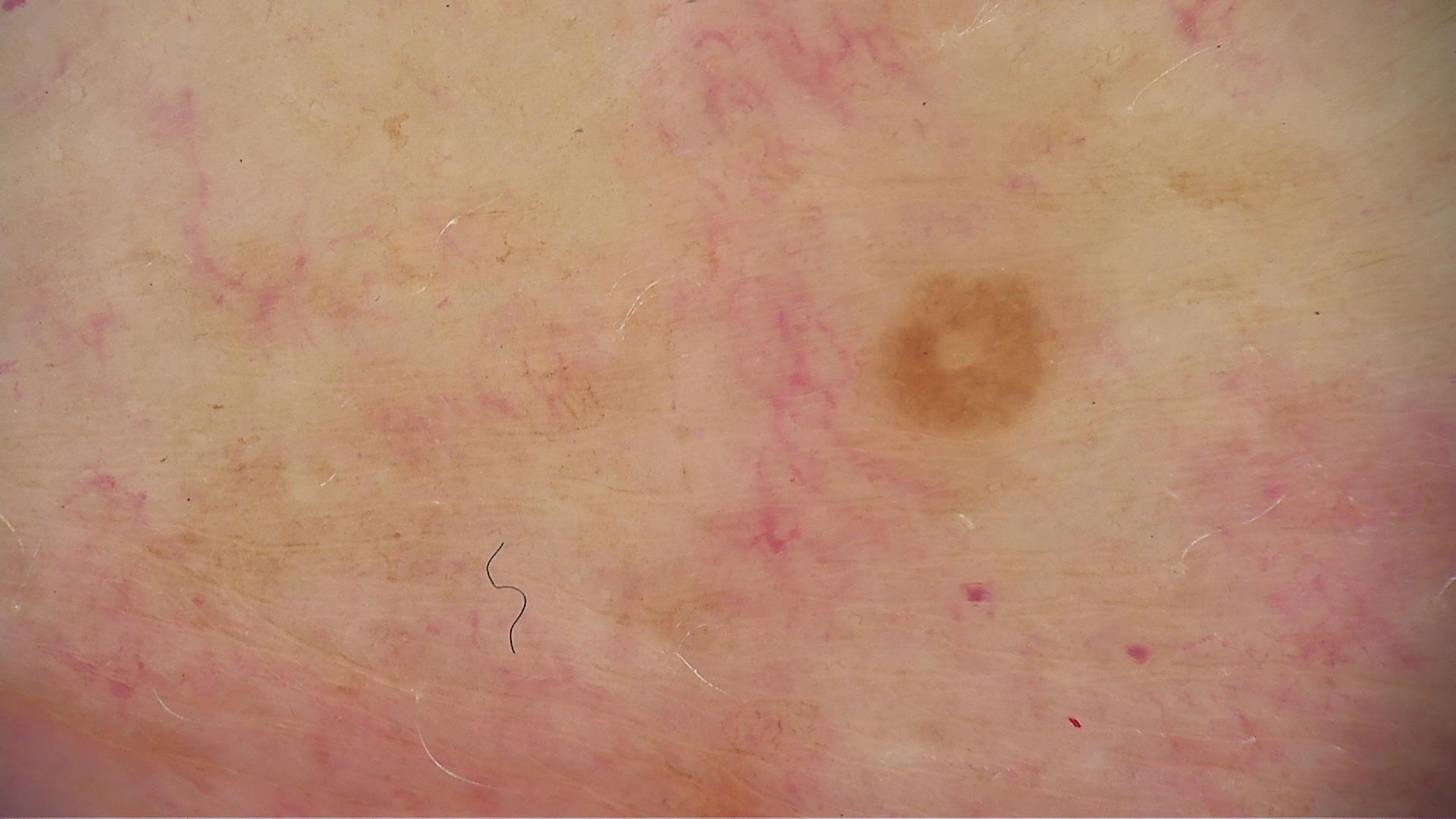image type = dermatoscopy
lesion type = keratinocytic
label = seborrheic keratosis (expert consensus)